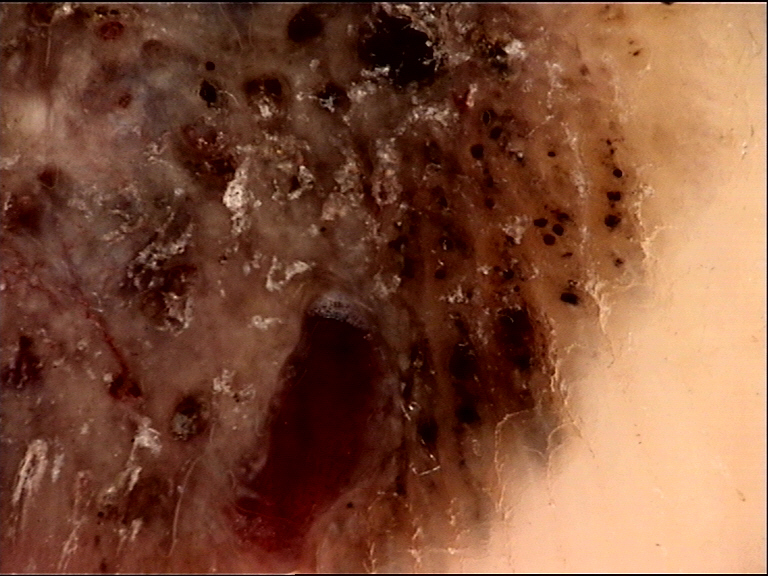Confirmed on histopathology as a malignancy — an acral nodular melanoma.